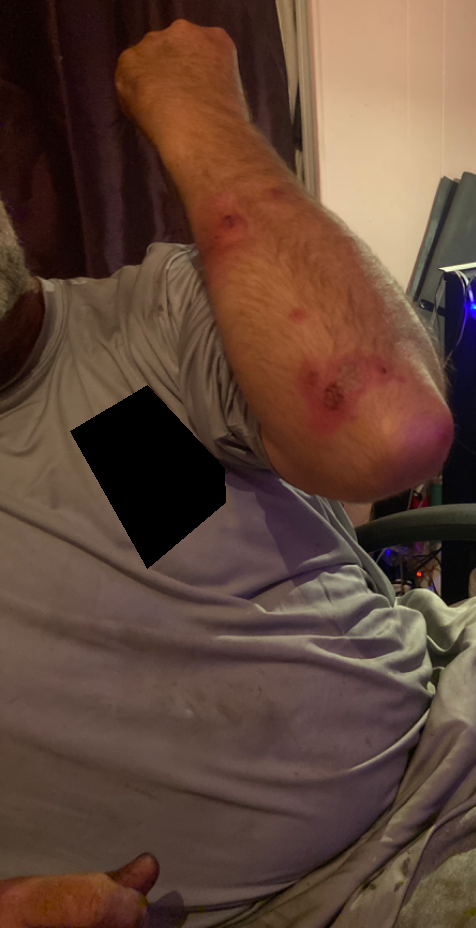assessment: could not be assessed; location: head or neck, leg and arm; photo taken: at a distance.